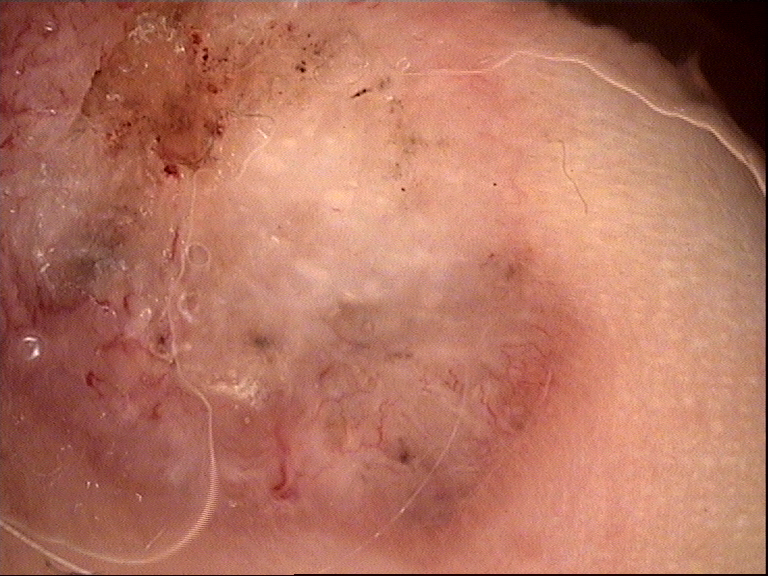image — dermatoscopy | diagnosis — basal cell carcinoma (biopsy-proven).